A dermoscopic photograph of a skin lesion.
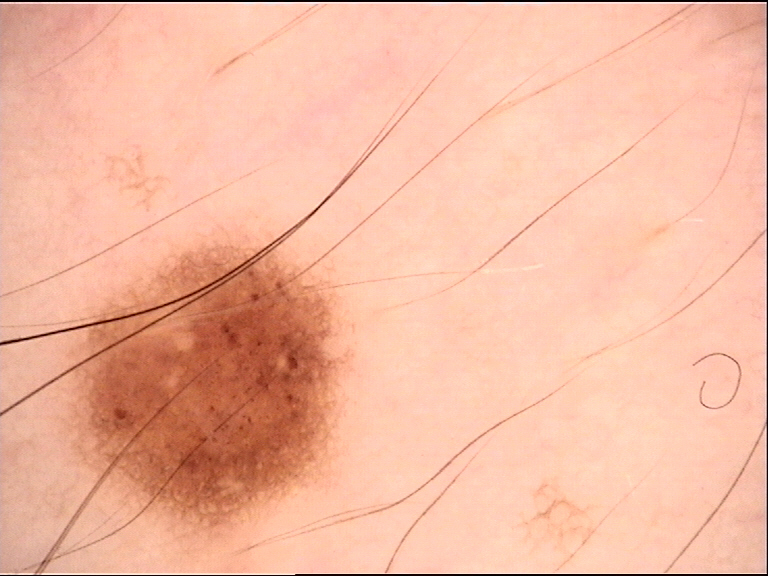Conclusion:
Diagnosed as a dysplastic junctional nevus.